A female patient 26 years of age; the patient says their skin reddens with sun exposure; the patient reports a history of sunbed use; a dermoscopy image of a skin lesion; the patient describes having numerous moles; imaged for a research study, with no referral diagnosis recorded:
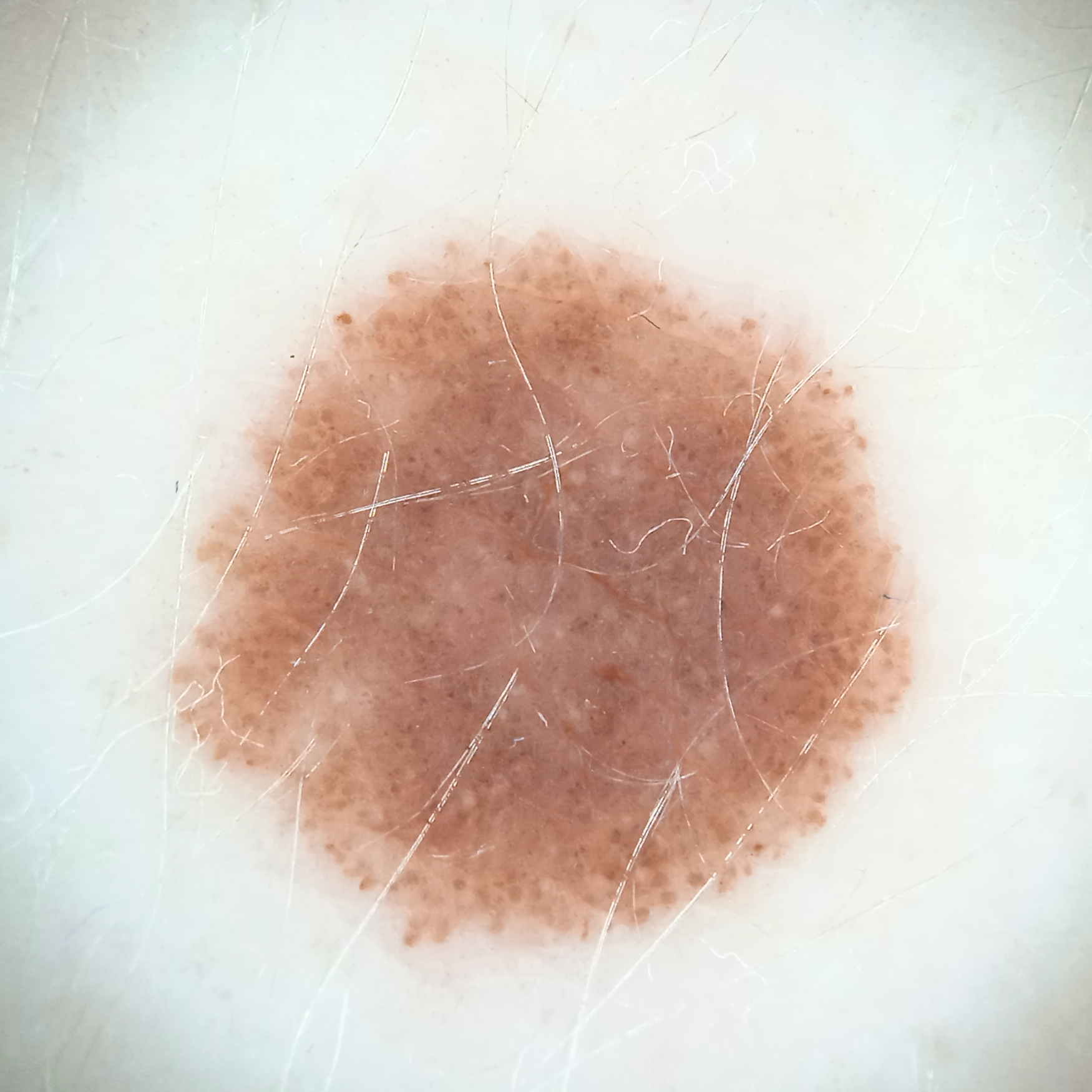anatomic site: the back; diagnosis: melanocytic nevus (dermatologist consensus).